A dermoscopic image of a skin lesion. Imaged for a research study, with no referral diagnosis recorded. The patient says their skin reddens painfully with sun exposure. A moderate number of moles by the patient's own estimate. By self-report, no personal history of cancer. A female patient 35 years old: 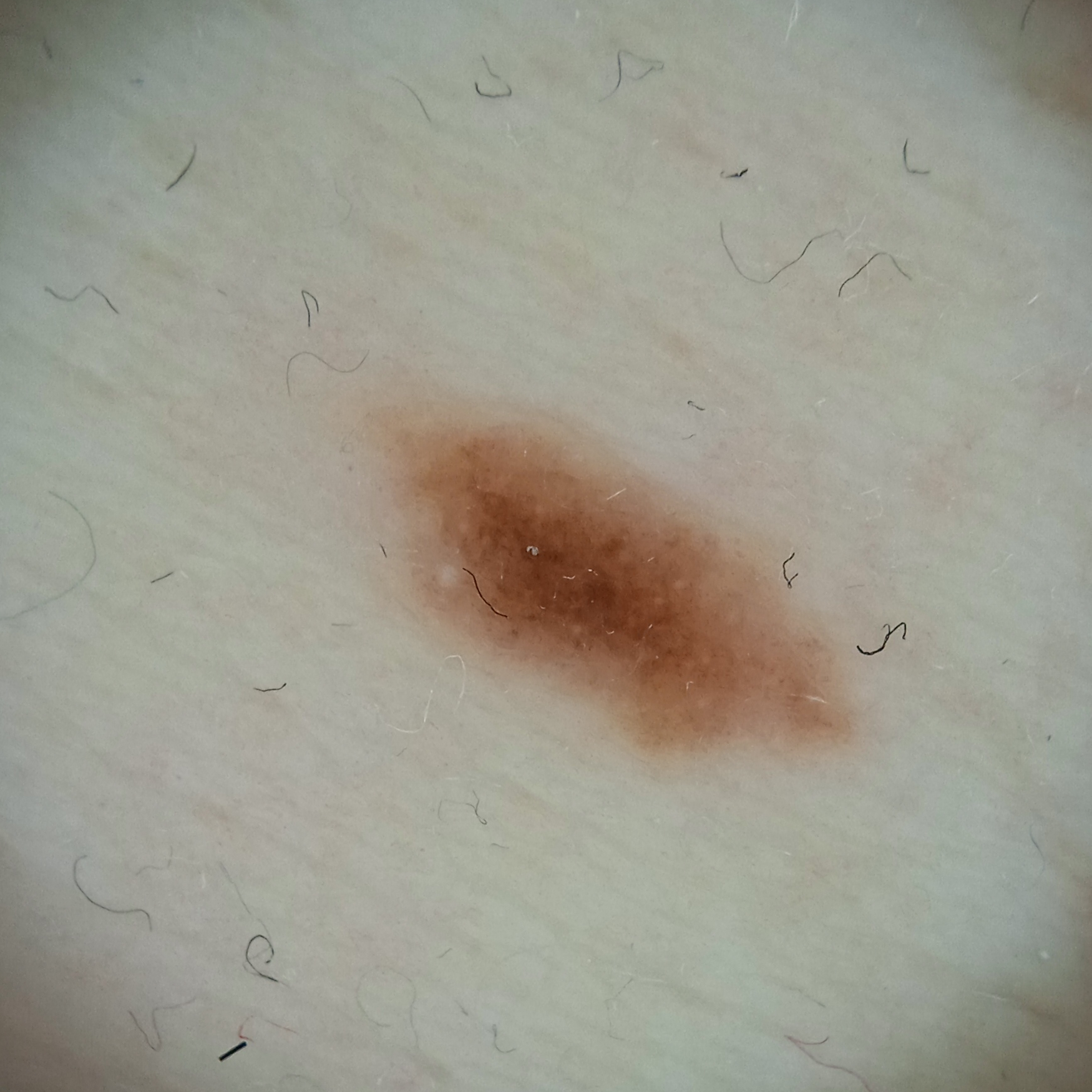| field | value |
|---|---|
| location | the torso |
| assessment | melanocytic nevus (dermatologist consensus) |